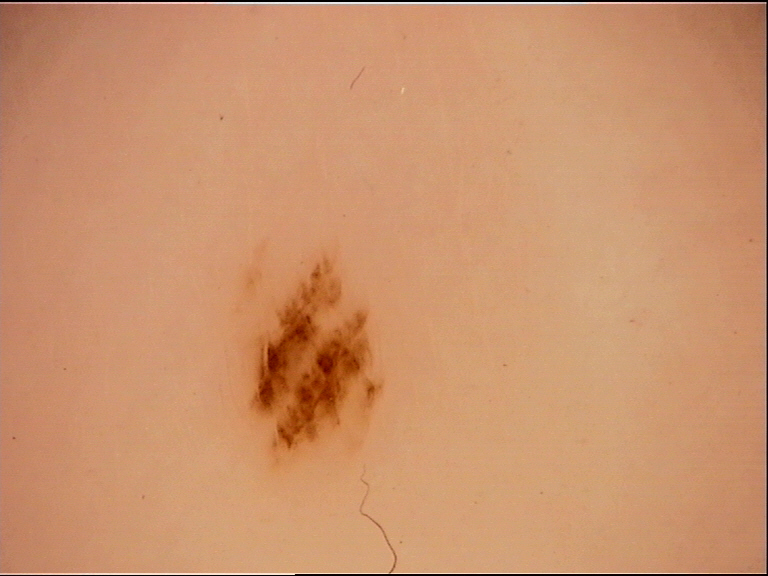Classified as an acral junctional nevus.